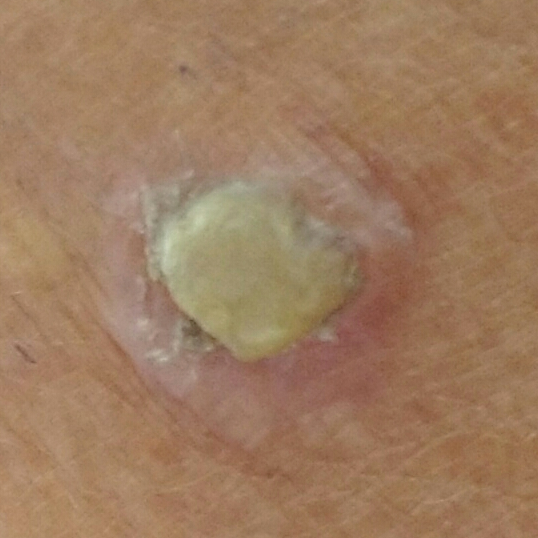Q: Any relevant history?
A: prior malignancy (patient or family)
Q: Tell me about the patient.
A: female, 73 years of age
Q: Skin phototype?
A: III
Q: How was this image acquired?
A: clinical photo
Q: What are the lesion's dimensions?
A: 10x7 mm
Q: What does the patient describe?
A: elevation, growth / no bleeding
Q: What is this lesion?
A: squamous cell carcinoma (biopsy-proven)